A dermoscopic photograph of a skin lesion.
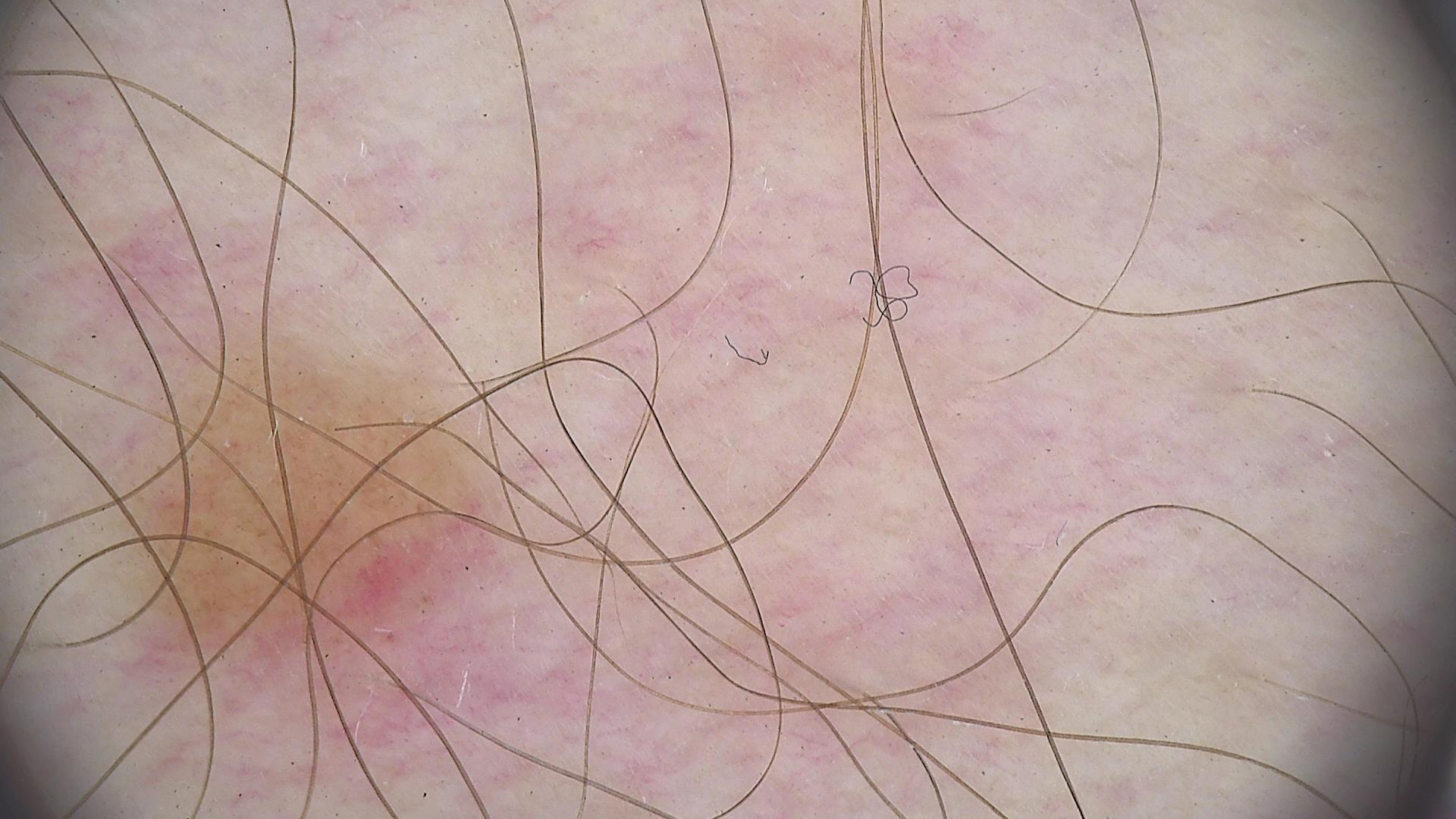Findings:
– diagnosis — junctional nevus (expert consensus)